A smartphone photograph of a skin lesion: 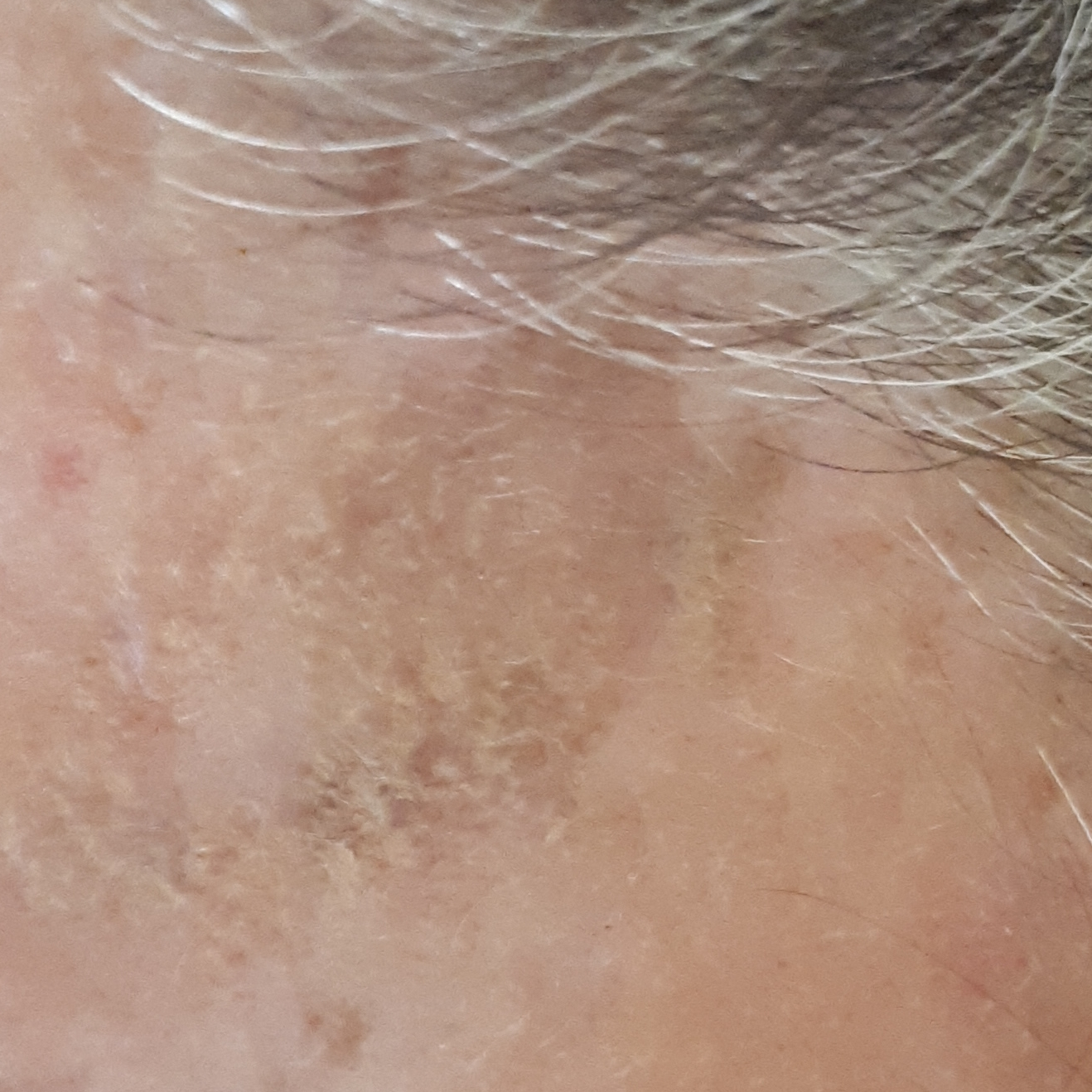- body site — the face
- diagnostic label — actinic keratosis (clinical consensus)